A dermoscopic image of a skin lesion: 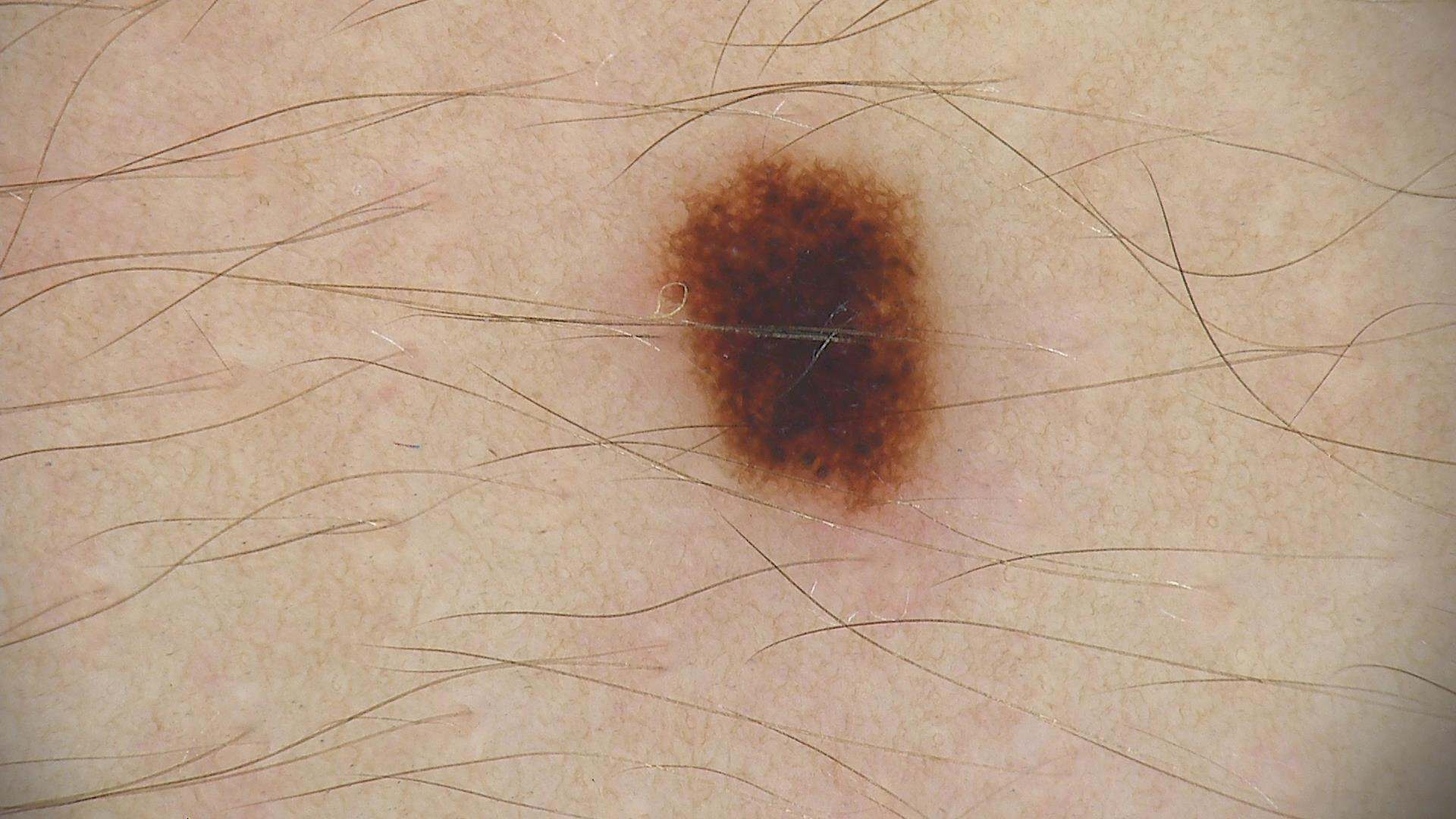diagnosis=dysplastic compound nevus (expert consensus)